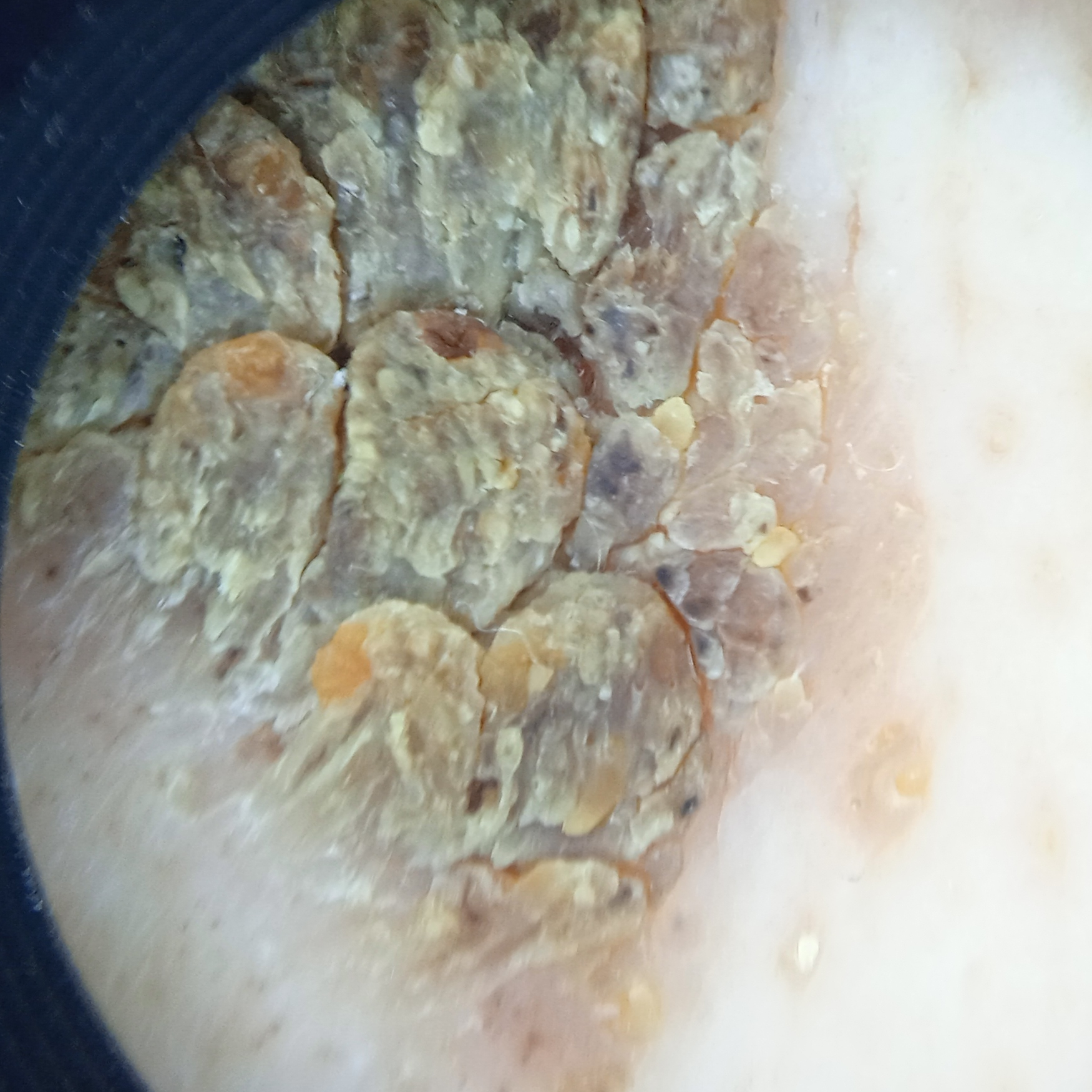imaging: dermoscopy; clinical context: research study (no referral diagnosis); patient: male, aged 65; location: the back; diagnostic label: seborrheic keratosis (dermatologist consensus).